A dermoscopic photograph of a skin lesion.
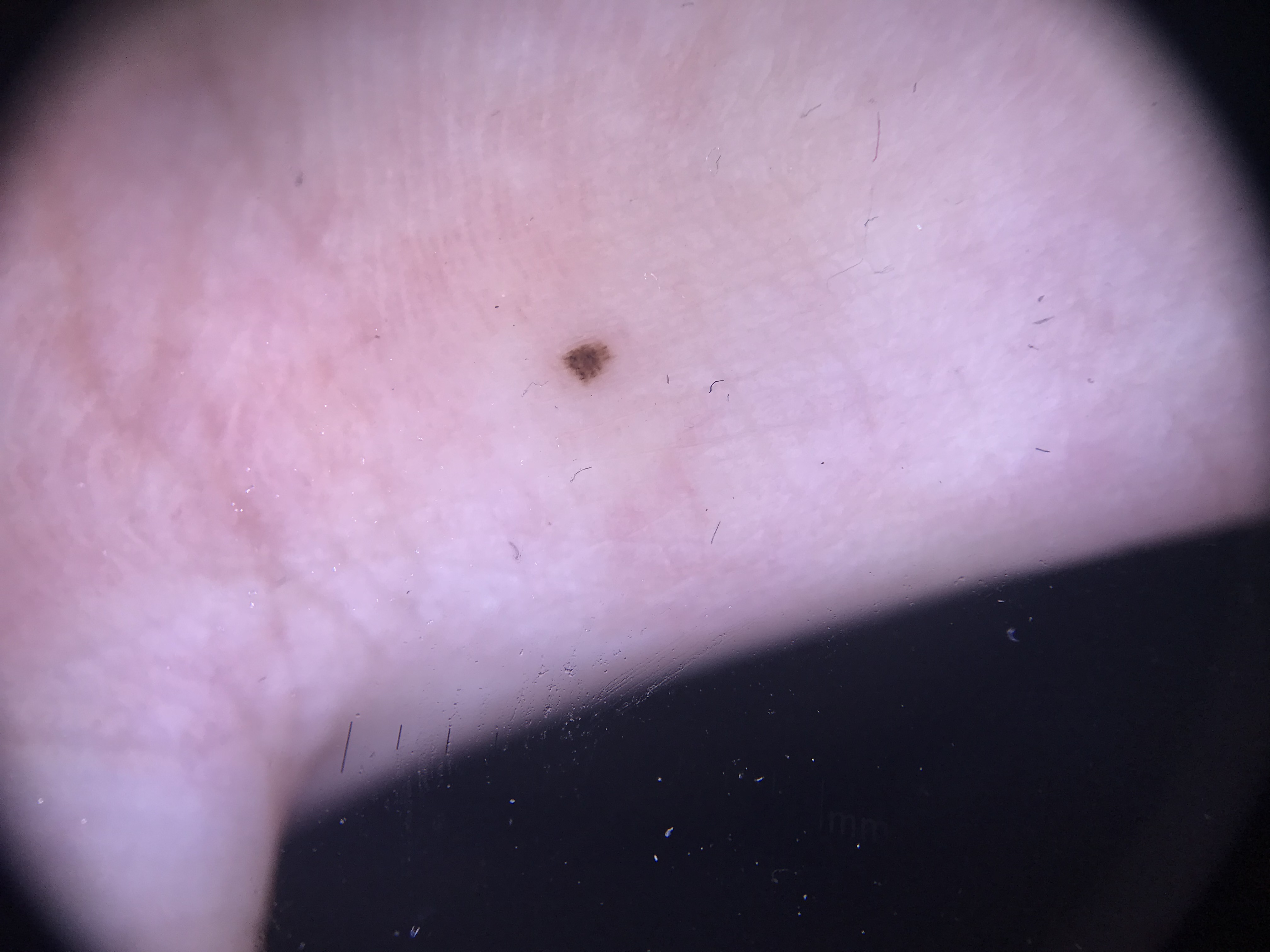The diagnostic label was a benign lesion — an acral dysplastic junctional nevus.